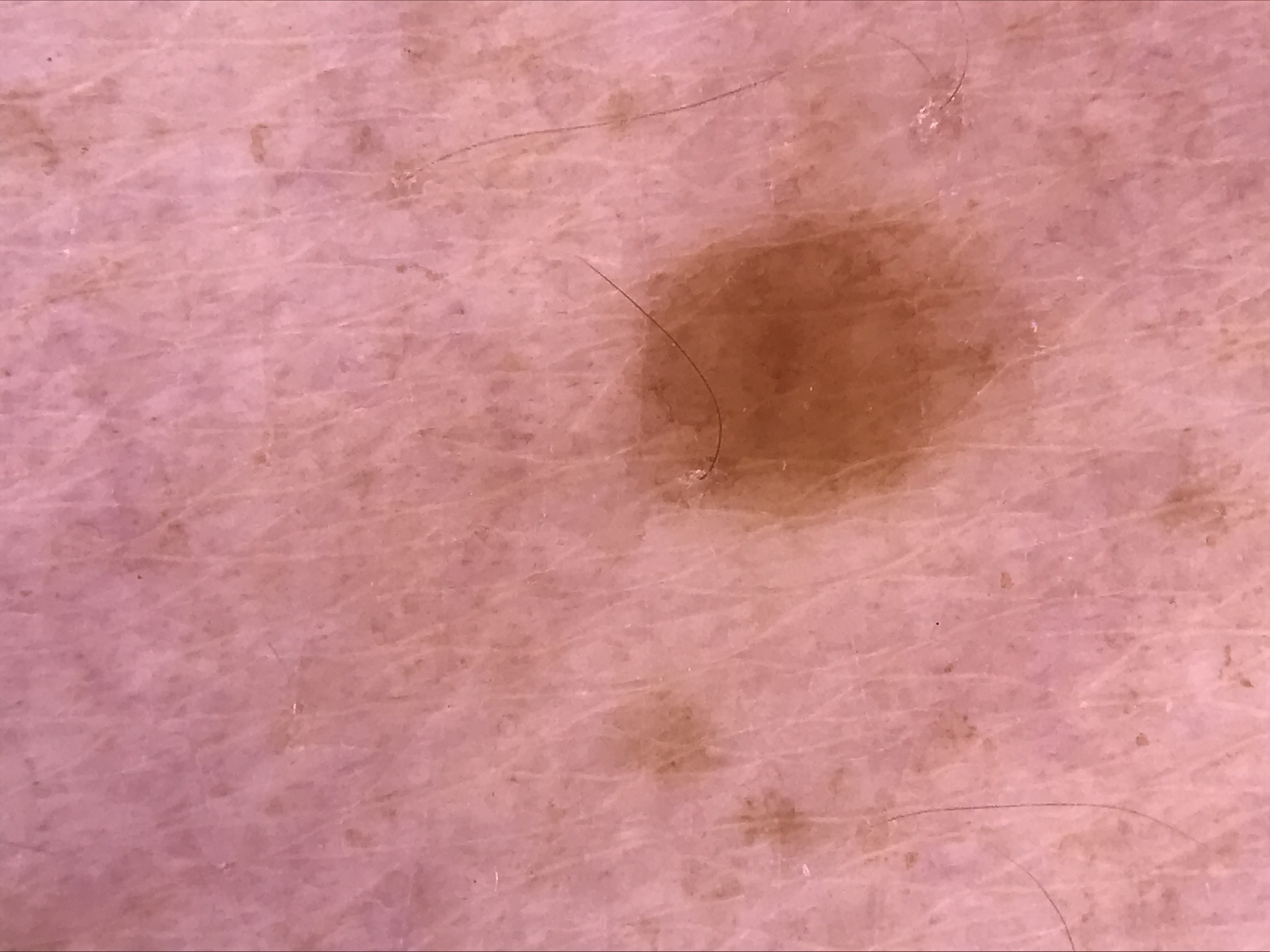Q: What kind of image is this?
A: dermatoscopy
Q: What is the lesion category?
A: banal
Q: What was the diagnostic impression?
A: junctional nevus (expert consensus)